The leg and arm are involved; female patient, age 18–29; a close-up photograph: 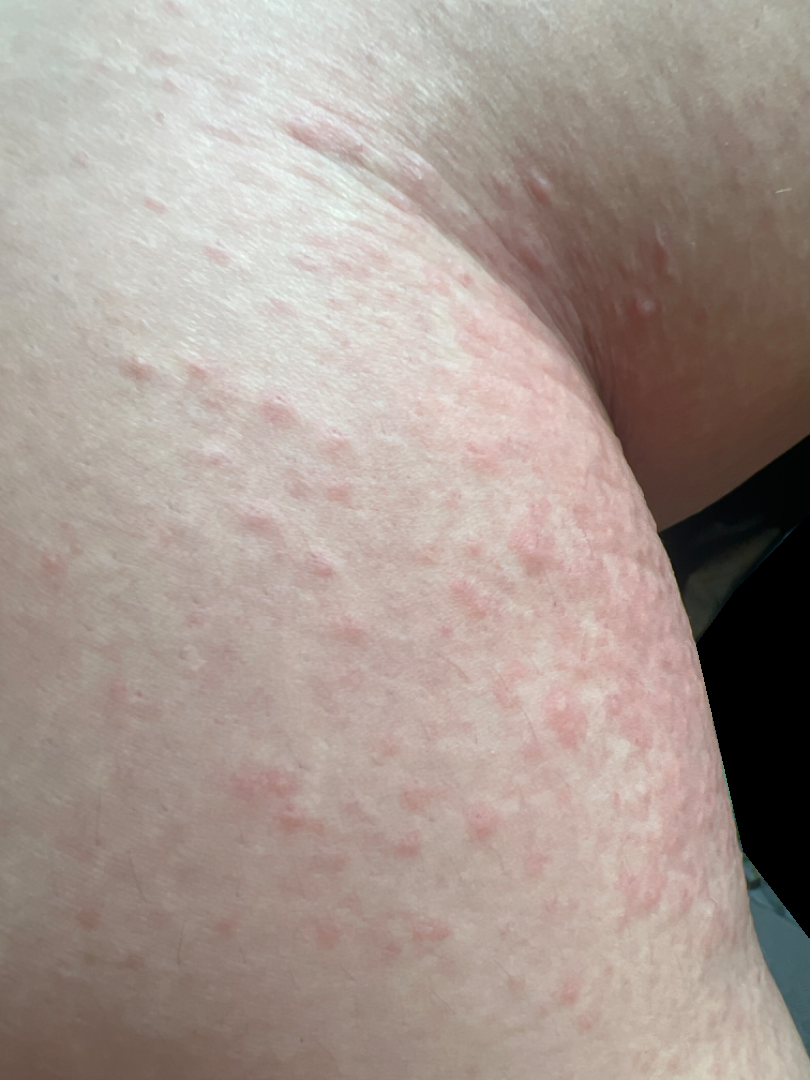<case>
  <assessment>could not be assessed</assessment>
</case>